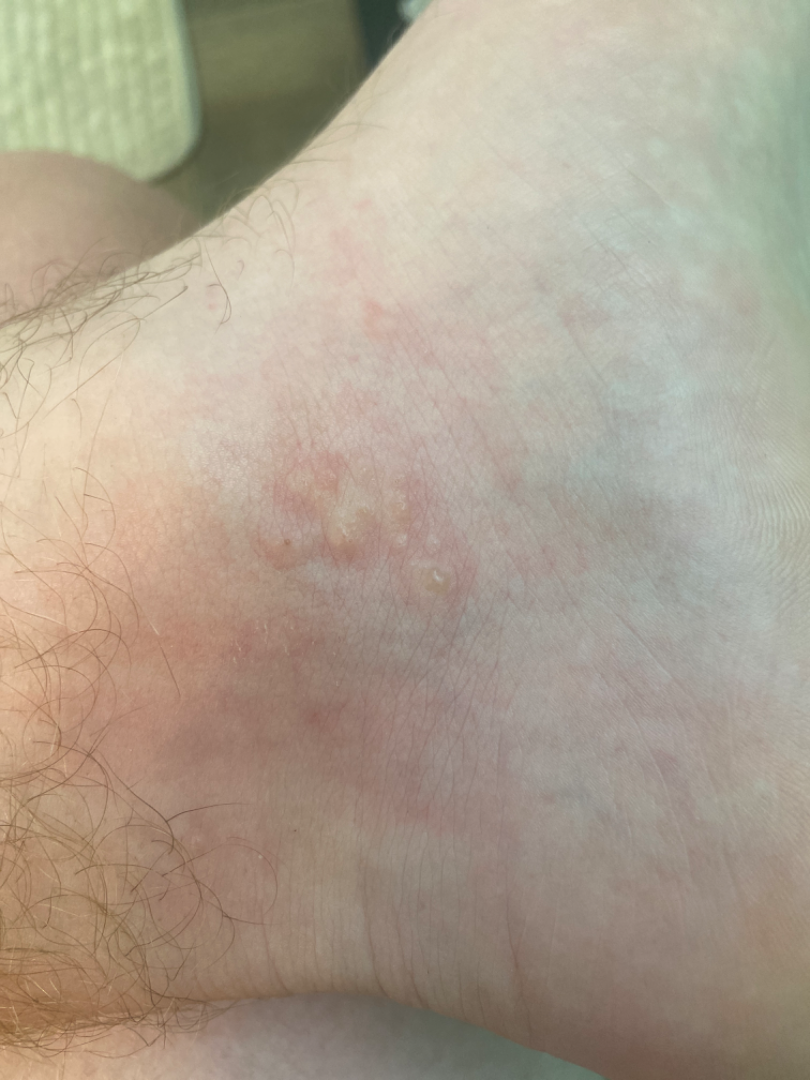assessment: not assessable
affected area: top or side of the foot
image framing: close-up